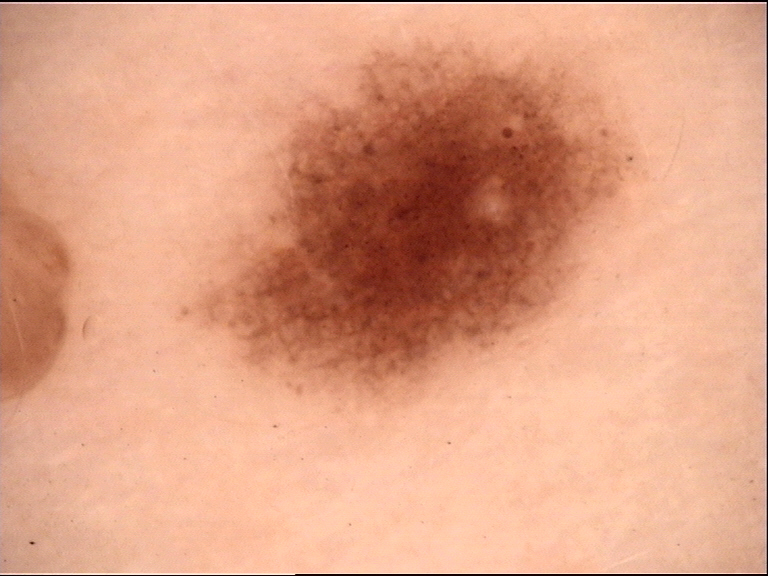The diagnosis was a benign lesion — a dysplastic junctional nevus.